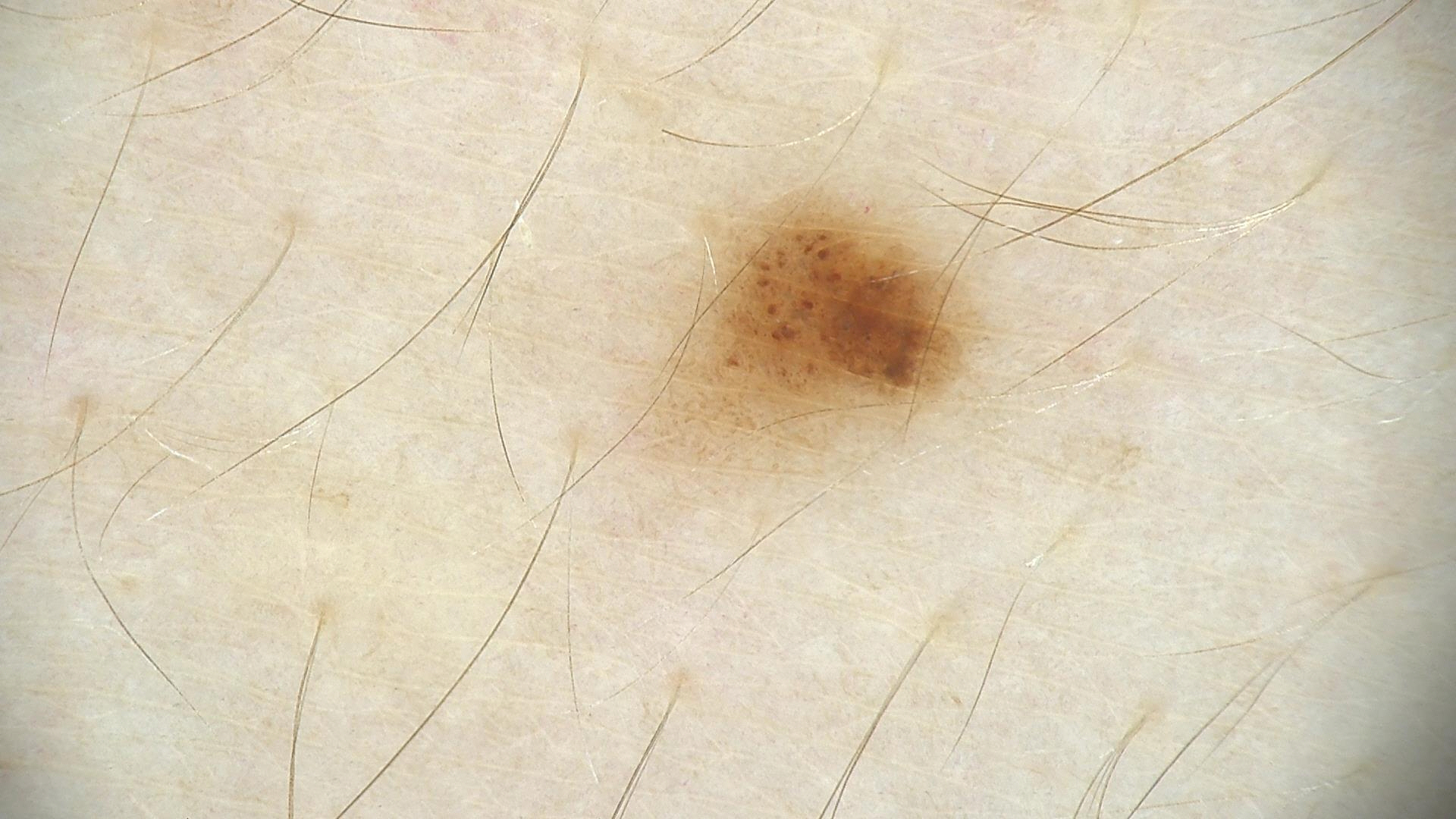Case:
Dermoscopy of a skin lesion.
Conclusion:
Labeled as a dysplastic junctional nevus.